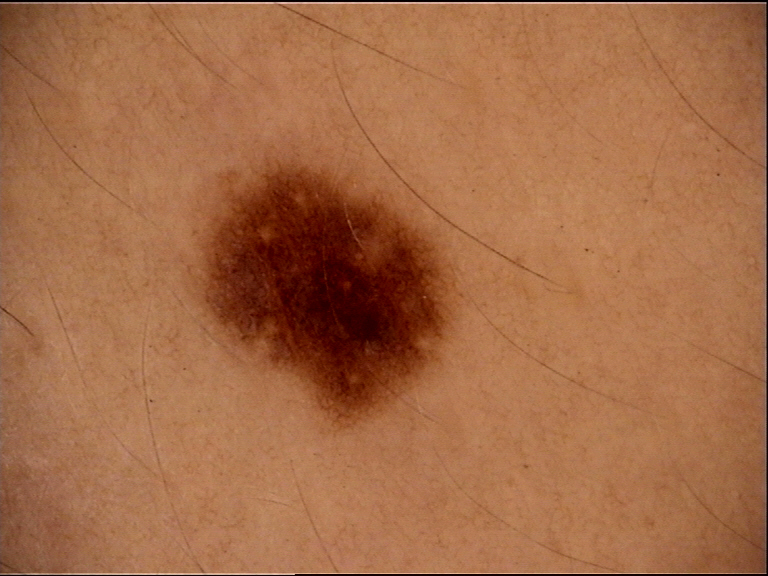Classified as a dysplastic junctional nevus.